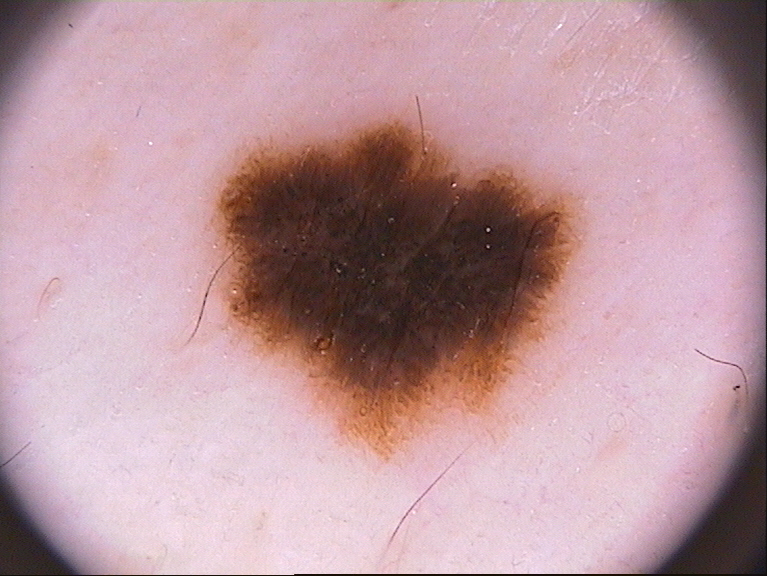The patient is female. A dermatoscopic image of a skin lesion. On dermoscopy, the lesion shows globules and pigment network, with no negative network, streaks, or milia-like cysts. The lesion occupies the region x1=204 y1=118 x2=588 y2=467. Diagnosed as a melanocytic nevus, a benign skin lesion.